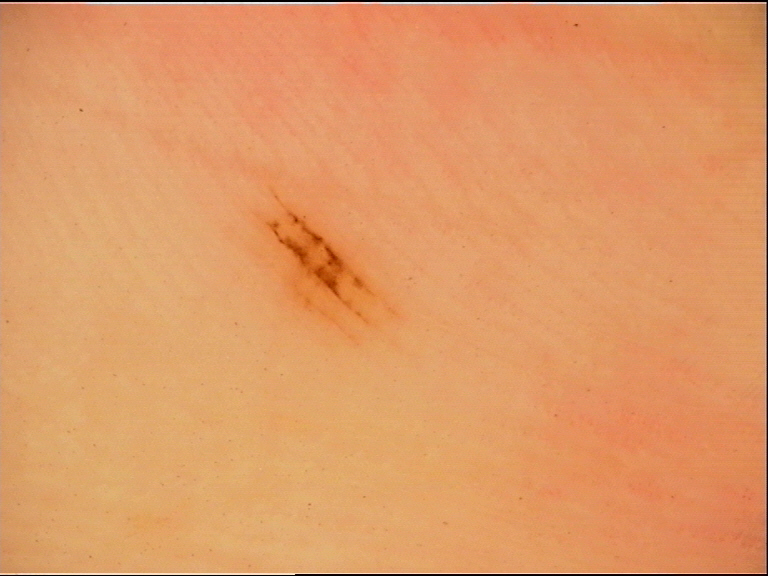diagnostic label: acral junctional nevus (expert consensus).